A skin lesion imaged with a dermatoscope.
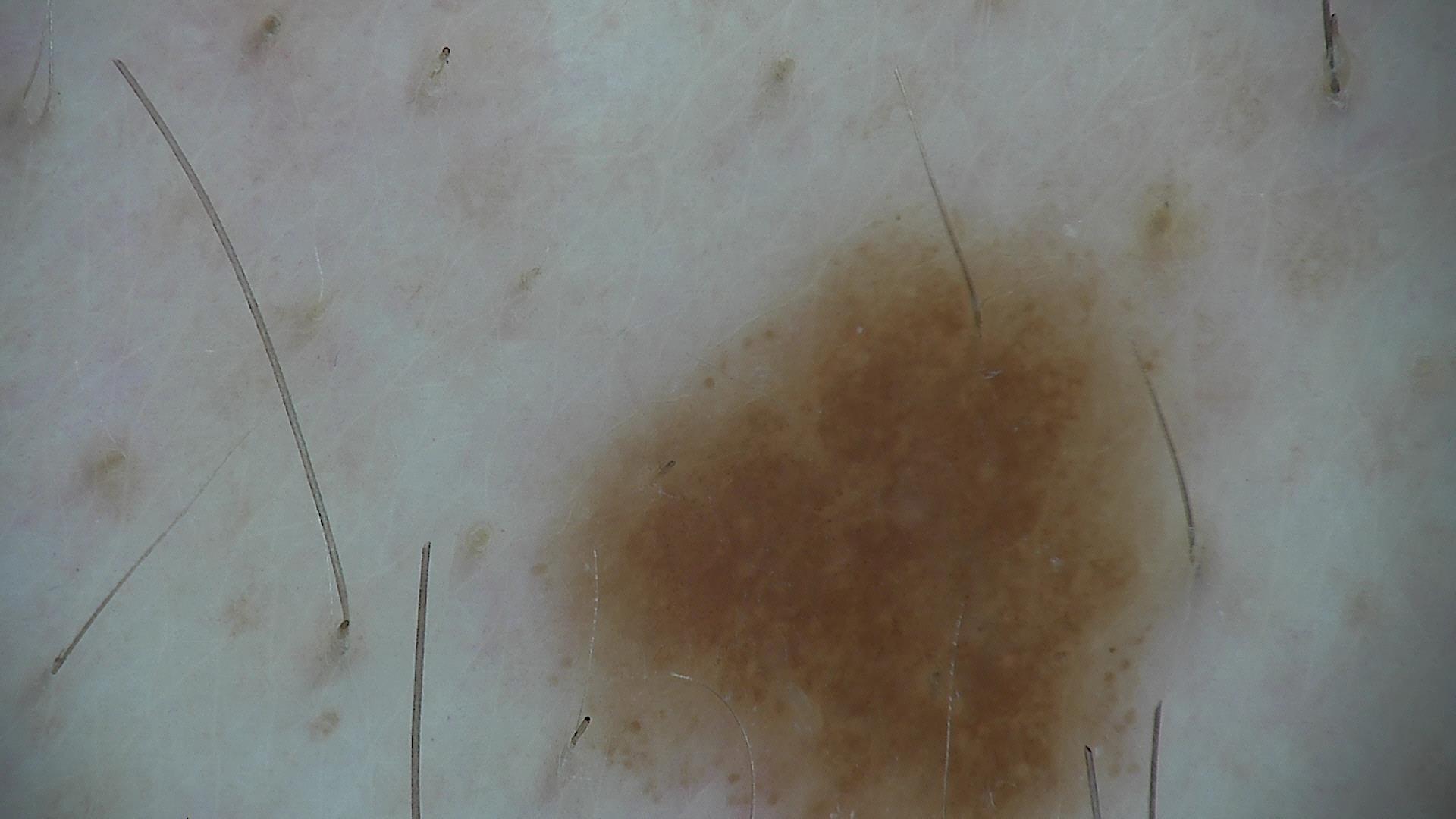  diagnosis:
    name: dysplastic junctional nevus
    code: jd
    malignancy: benign
    super_class: melanocytic
    confirmation: expert consensus